Reported duration is about one day · the patient considered this acne · the photo was captured at a distance: 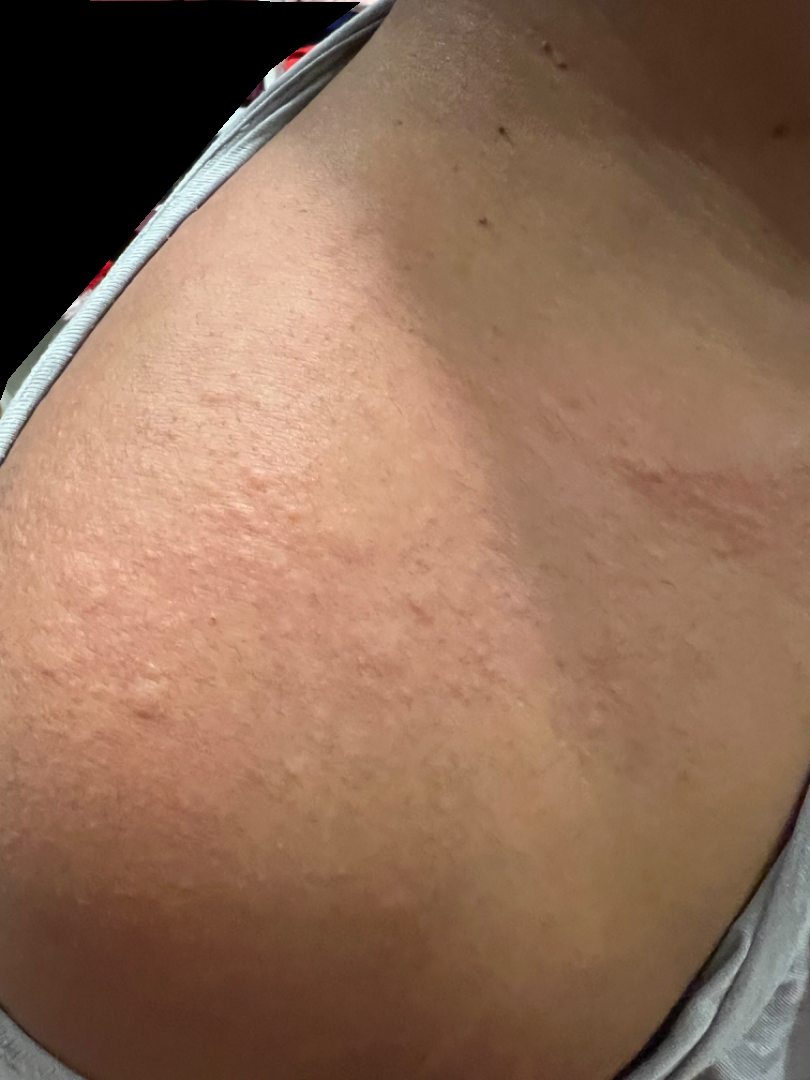A single dermatologist reviewed the case: favoring Urticaria; possibly Allergic Contact Dermatitis.